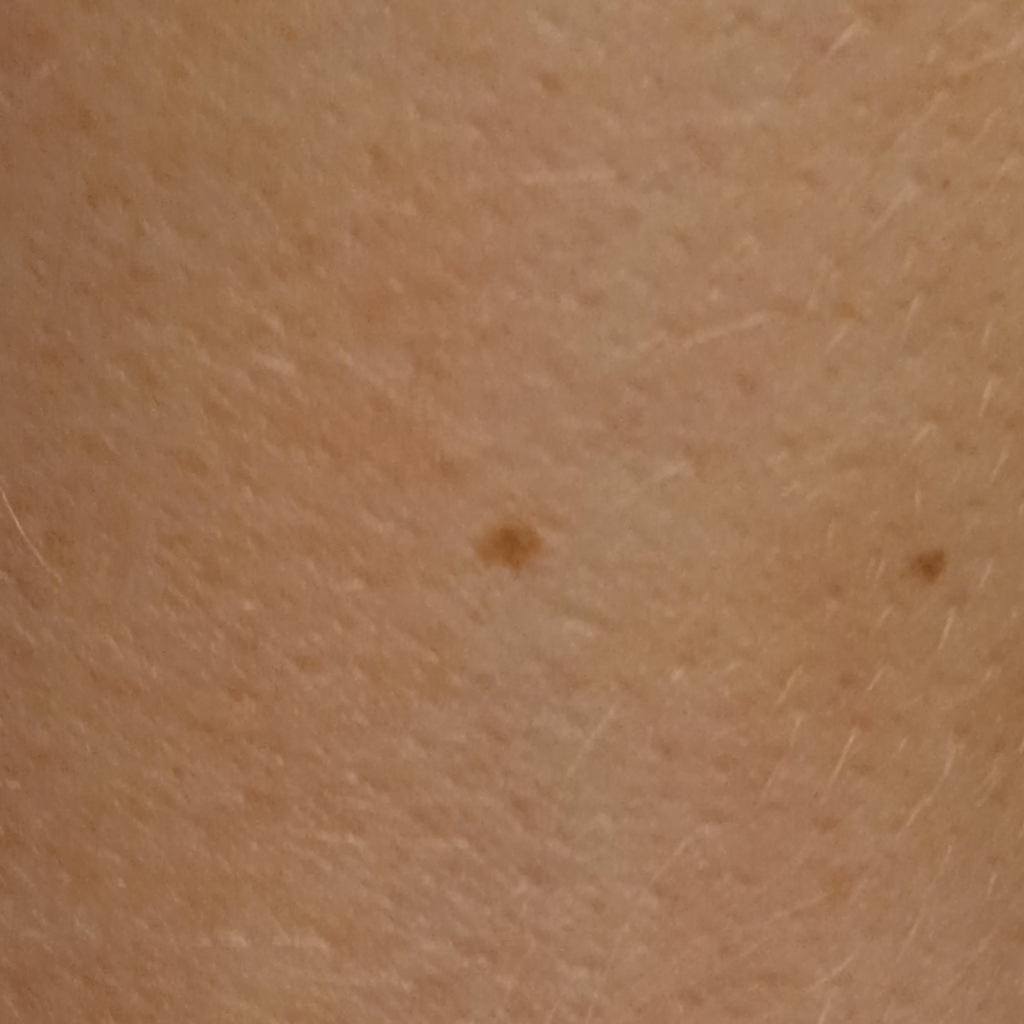Clinical context: Imaged for a research study, with no referral diagnosis recorded. A macroscopic clinical photograph of a skin lesion. The patient describes having a moderate number of moles. The patient says their skin reddens painfully with sun exposure. A female subject age 50. The lesion is located on an arm. The lesion is about 2 mm across. Impression: The lesion was assessed as a melanocytic nevus.